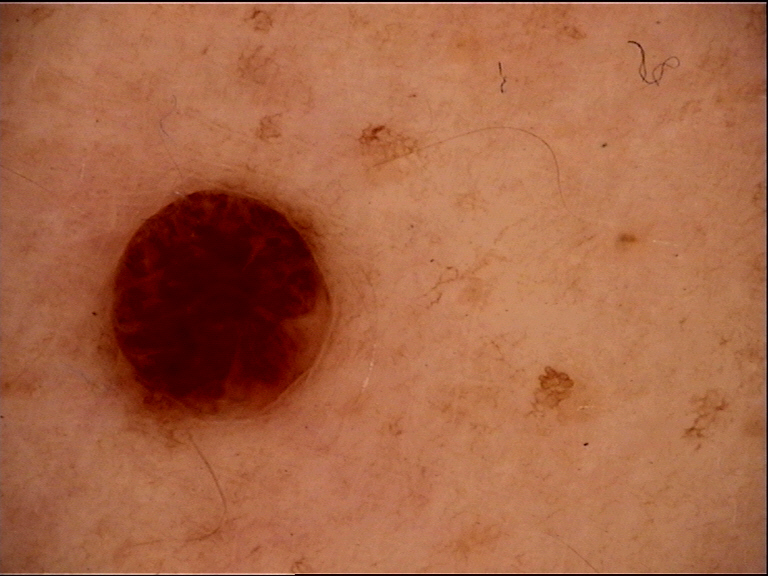assessment=dermal nevus (expert consensus).